A male subject 56 years of age · history notes alcohol use and pesticide exposure: 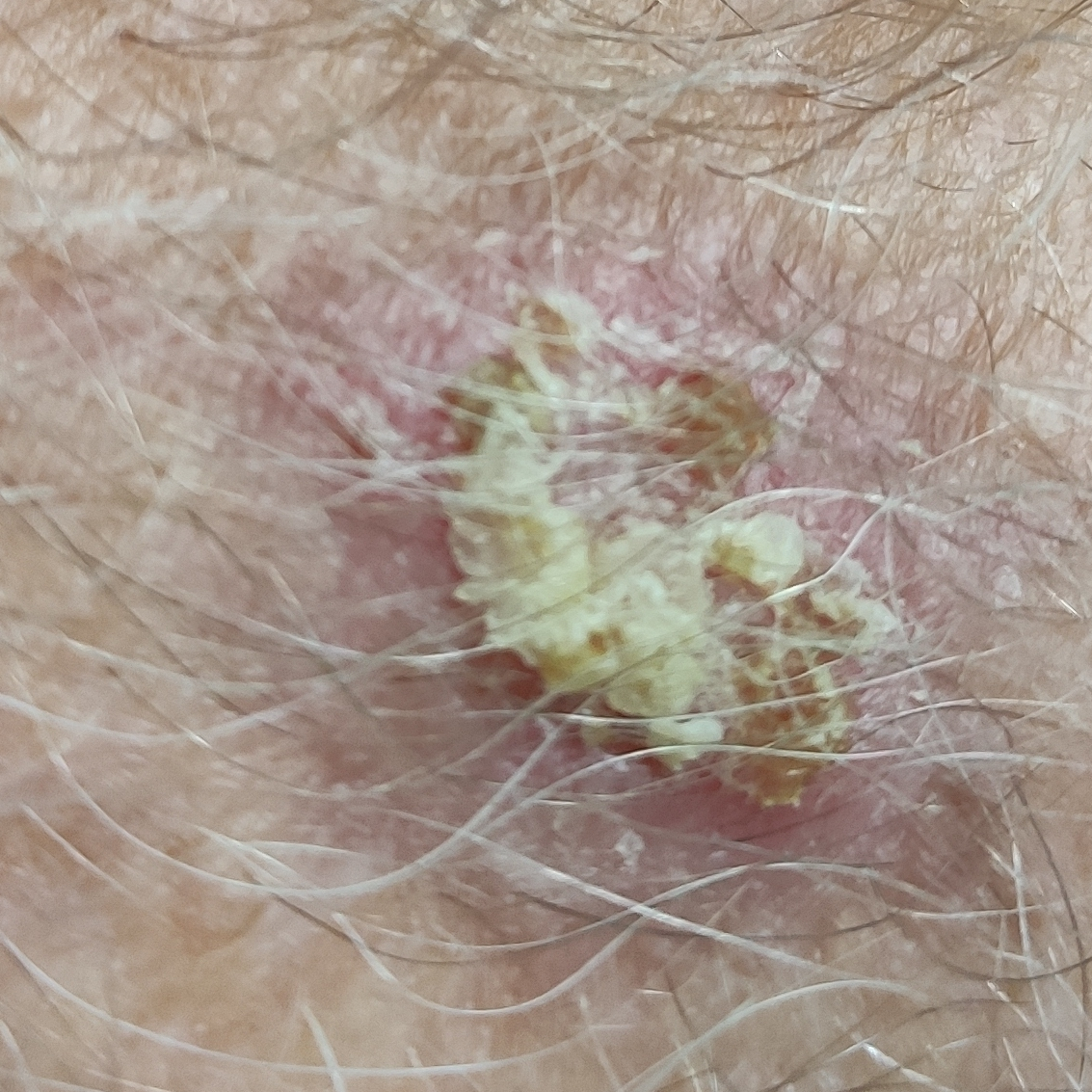{
  "lesion_location": "a forearm",
  "lesion_size": {
    "diameter_1_mm": 10.0,
    "diameter_2_mm": 10.0
  },
  "symptoms": {
    "present": [
      "elevation",
      "change in appearance"
    ]
  },
  "diagnosis": {
    "name": "actinic keratosis",
    "code": "ACK",
    "malignancy": "indeterminate",
    "confirmation": "clinical consensus"
  }
}